Fitzpatrick skin type II; non-clinician graders estimated Monk Skin Tone 2 or 3 (two reviewer pools). A close-up photograph — 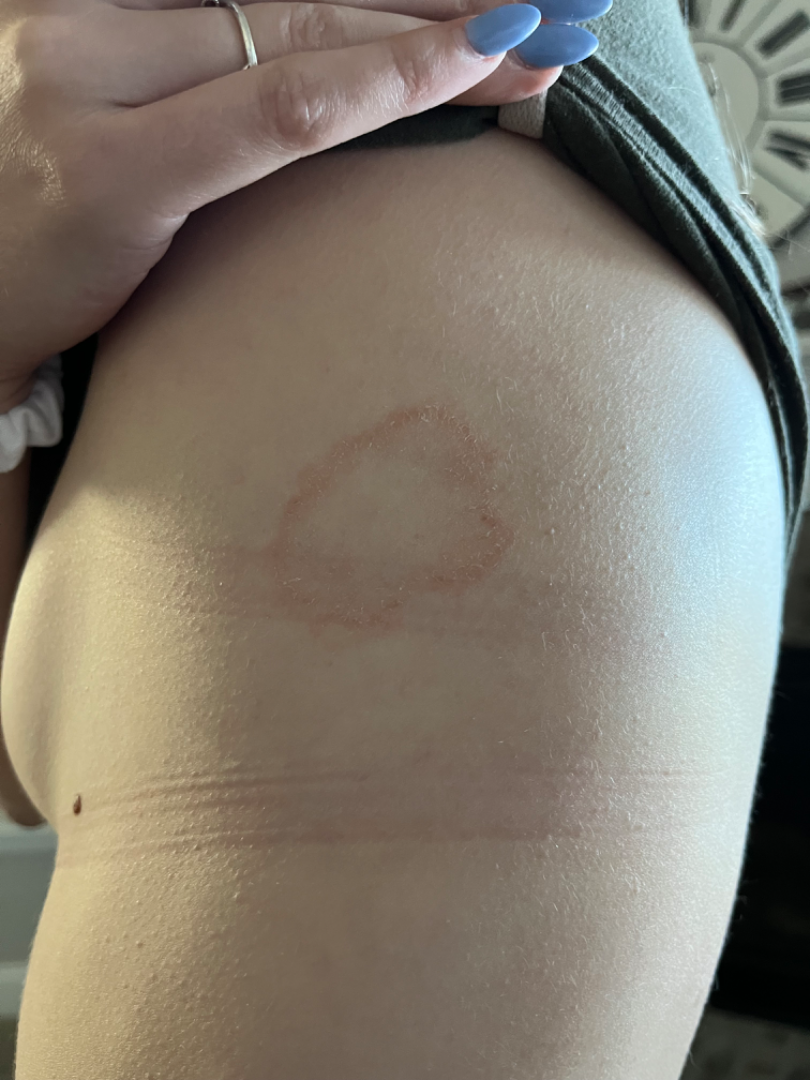Findings:
Favoring Tinea; an alternative is Erythema annulare centrifugum; also on the differential is Porokeratosis.